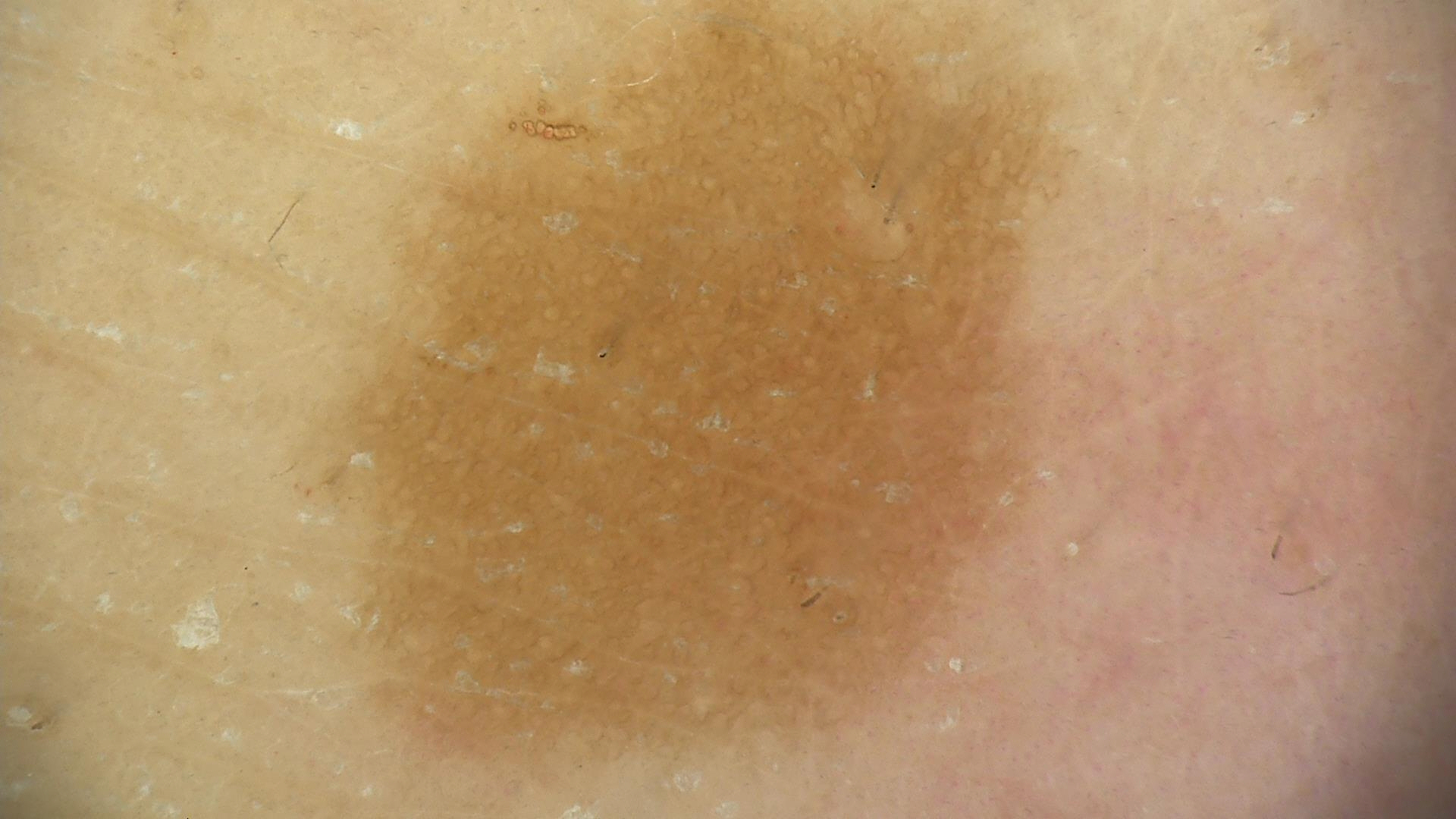diagnosis:
  name: solar lentigo
  code: sl
  malignancy: benign
  super_class: melanocytic
  confirmation: expert consensus